No relevant systemic symptoms · located on the top or side of the foot · Fitzpatrick V; human graders estimated 3 on the Monk Skin Tone · symptoms reported: bothersome appearance · an image taken at an angle · the patient notes the condition has been present for more than five years · texture is reported as raised or bumpy · the patient described the issue as a nail problem — 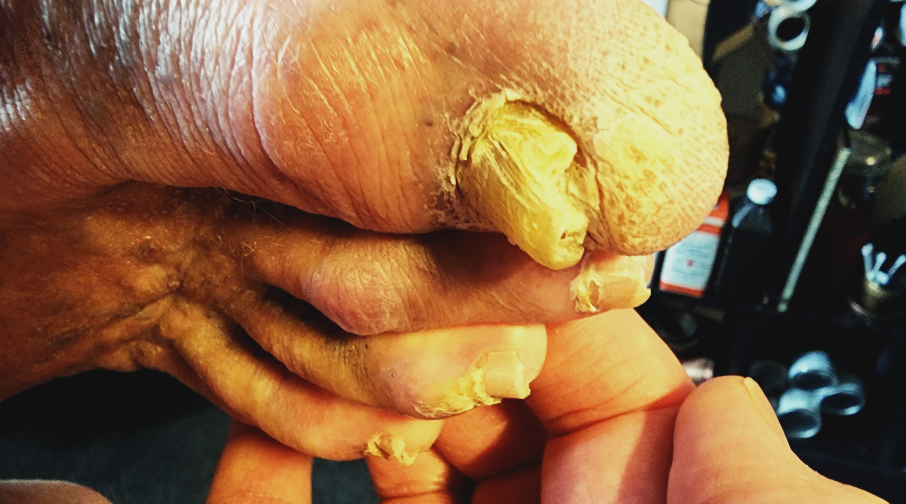differential diagnosis: Onychomycosis (leading); Psoriasis (lower probability); Pachyonychia congenita (lower probability); Lichen planus/lichenoid eruption (lower probability)